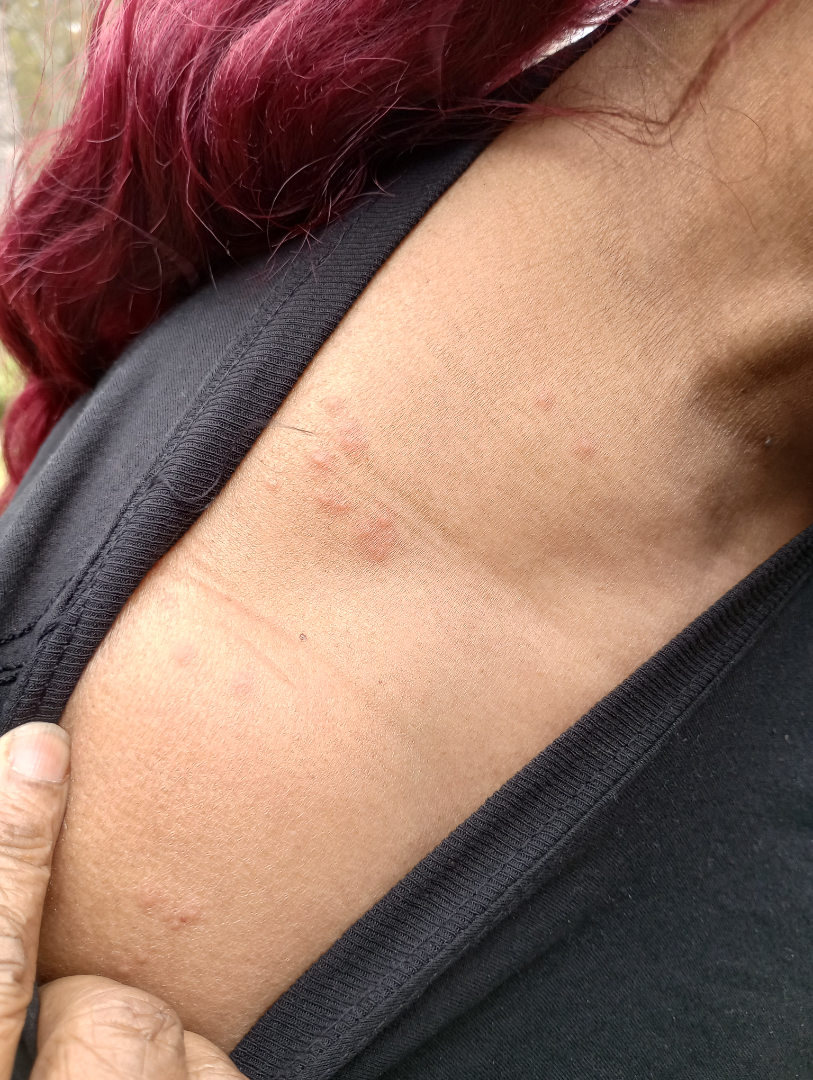History:
The photograph is a close-up of the affected area.
Impression:
Insect Bite (favored); Herpes Zoster (possible); Eczema (possible).